The arm is involved · close-up view:
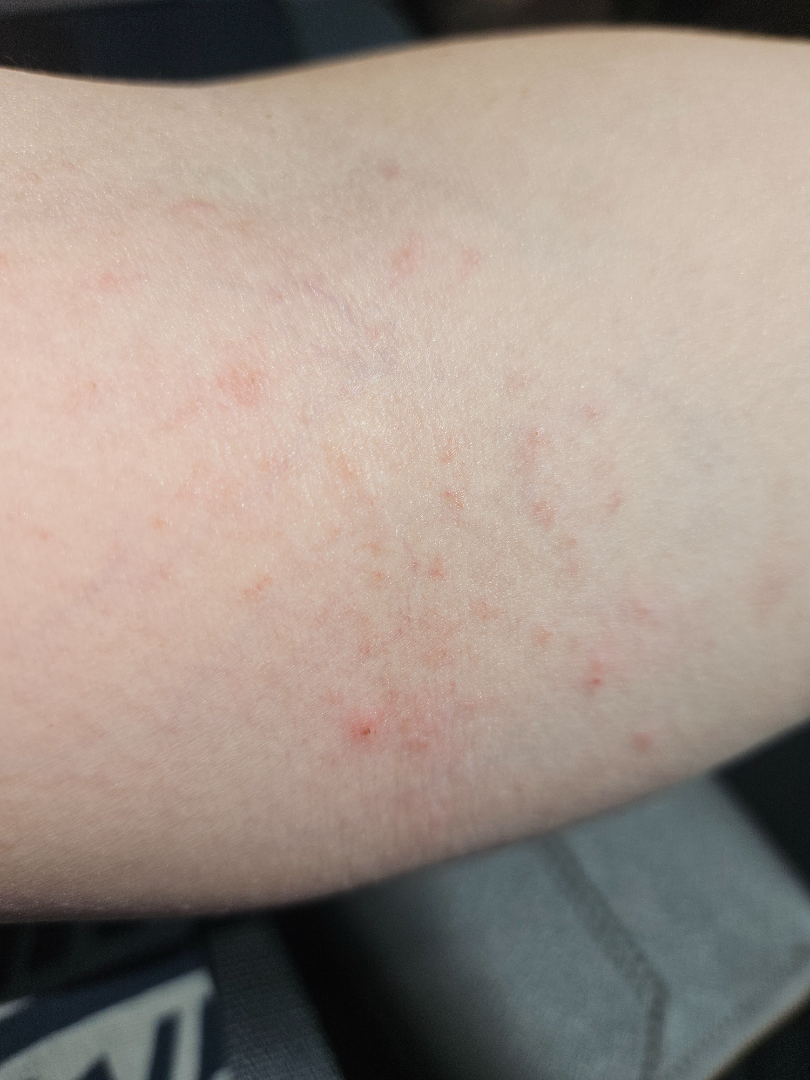<report>
  <patient_category>a rash</patient_category>
  <symptoms>burning, itching</symptoms>
  <duration>less than one week</duration>
  <differential>
    <leading>Eczema</leading>
  </differential>
</report>